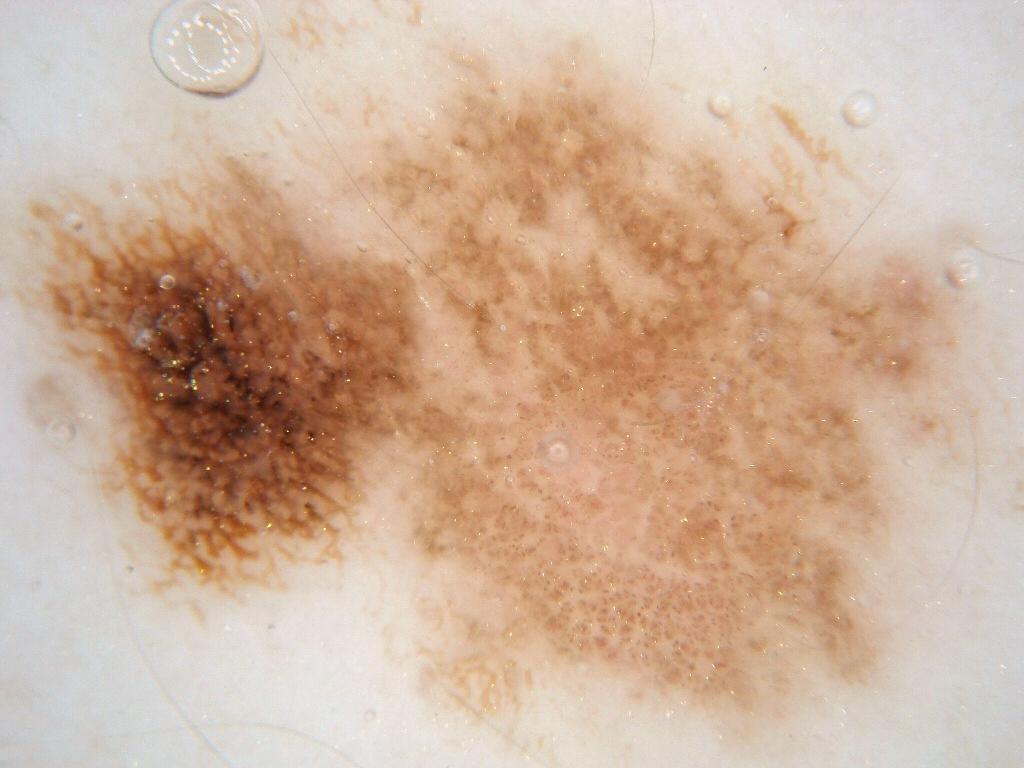A dermatoscopic image of a skin lesion. The lesion spans essentially the entire dermoscopic field. Expert review diagnosed this as a benign lesion.